A female subject age 47; the patient was assessed as Fitzpatrick skin type III; a smartphone photograph of a skin lesion; by history, prior malignancy (patient or family):
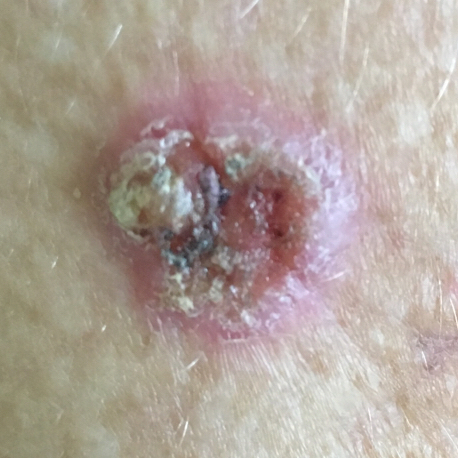lesion_location: a forearm
lesion_size:
  diameter_1_mm: 15.0
  diameter_2_mm: 13.0
diagnosis:
  name: basal cell carcinoma
  code: BCC
  malignancy: malignant
  confirmation: histopathology